A dermoscopic image of a skin lesion.
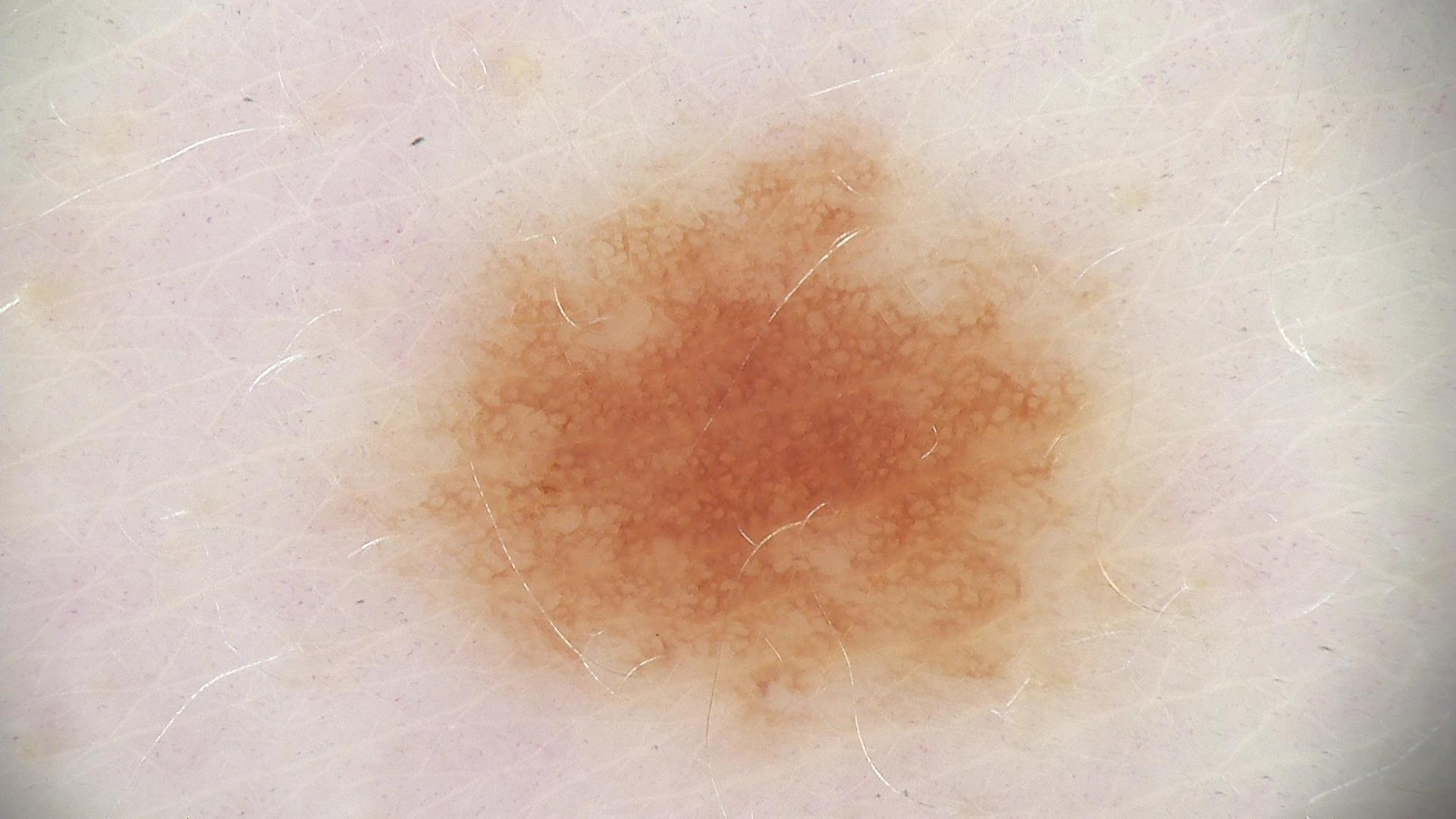  diagnosis:
    name: dysplastic junctional nevus
    code: jd
    malignancy: benign
    super_class: melanocytic
    confirmation: expert consensus